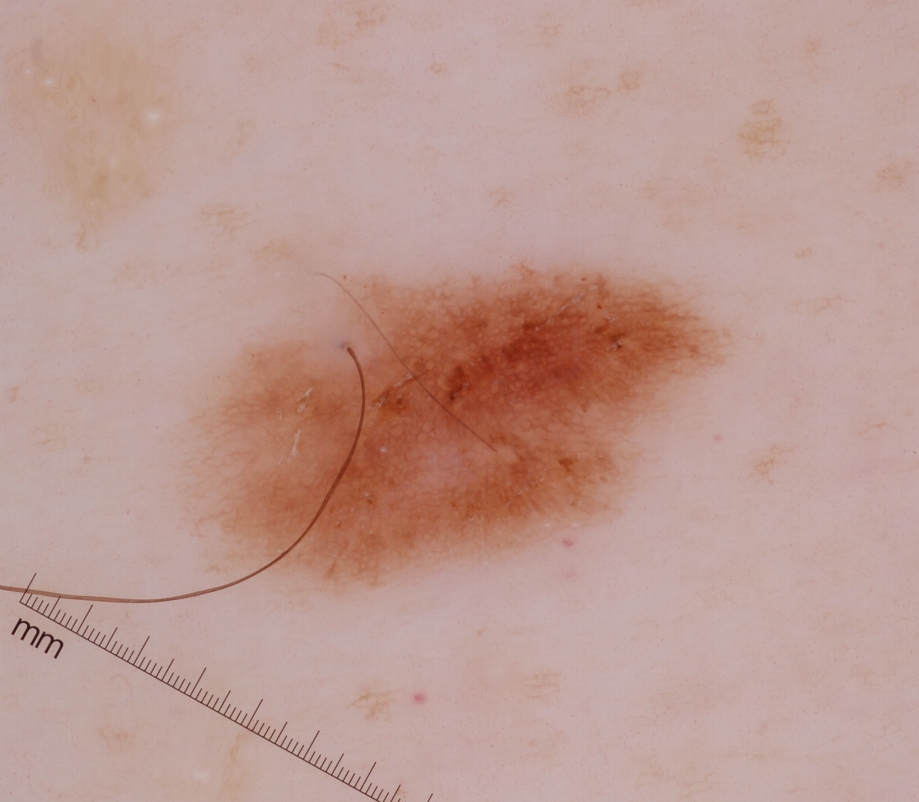| feature | finding |
|---|---|
| image type | dermoscopy |
| dermoscopic features | pigment network and globules; absent: streaks, negative network, and milia-like cysts |
| location | <box>152, 257, 755, 607</box> |
| diagnosis | a melanocytic nevus |